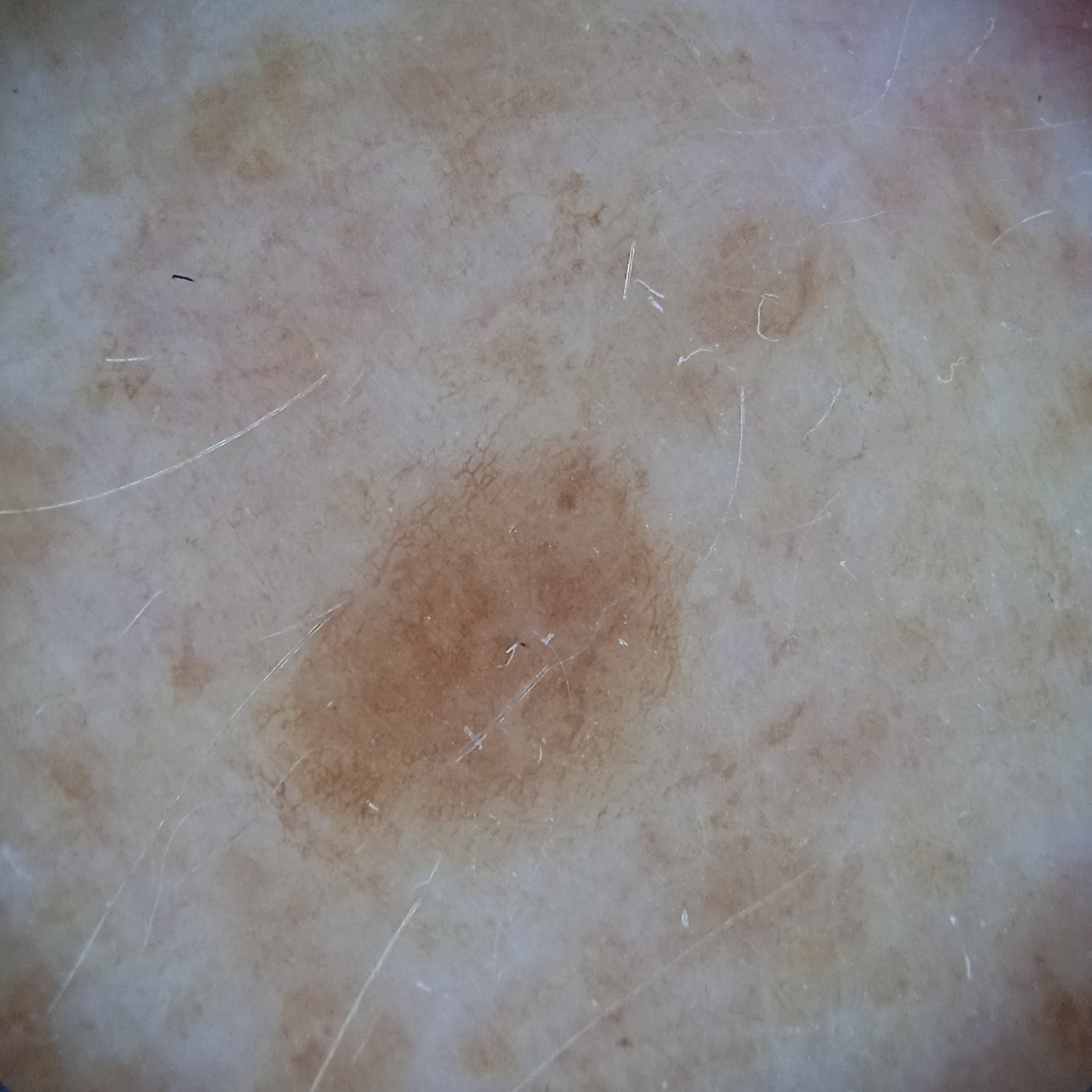subject: female, 78 years old | imaging: dermoscopic image | referral context: research study (no referral diagnosis) | location: an arm | size: 5.3 mm | assessment: seborrheic keratosis (dermatologist consensus).